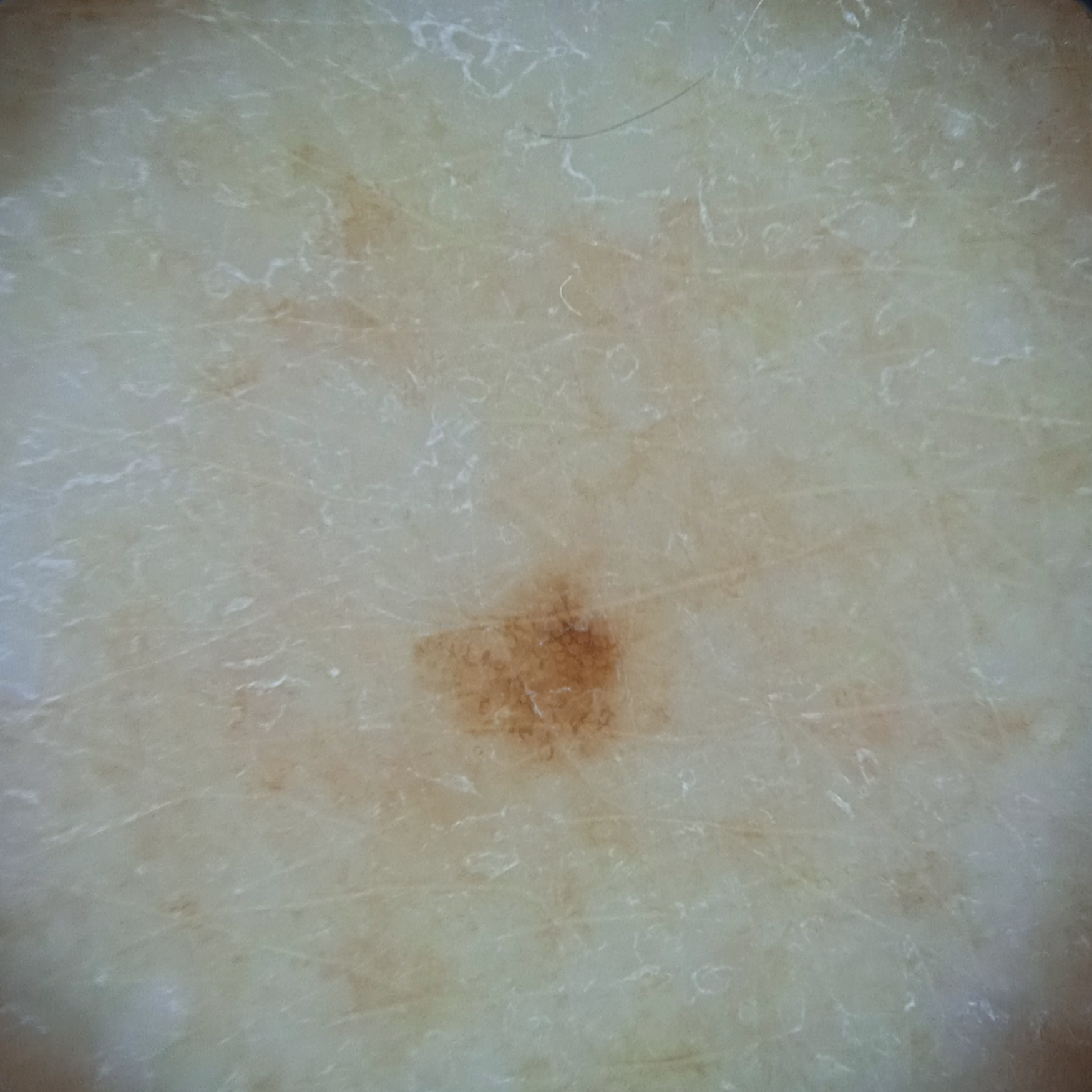Q: What are the relevant risk factors?
A: no personal history of cancer
Q: What is the patient's nevus burden?
A: few melanocytic nevi overall
Q: What kind of image is this?
A: dermoscopic image
Q: How does the patient's skin react to sun?
A: skin tans without first burning
Q: What is the anatomic site?
A: an arm
Q: What was the diagnosis?
A: melanocytic nevus (dermatologist consensus)